The photograph is a close-up of the affected area: 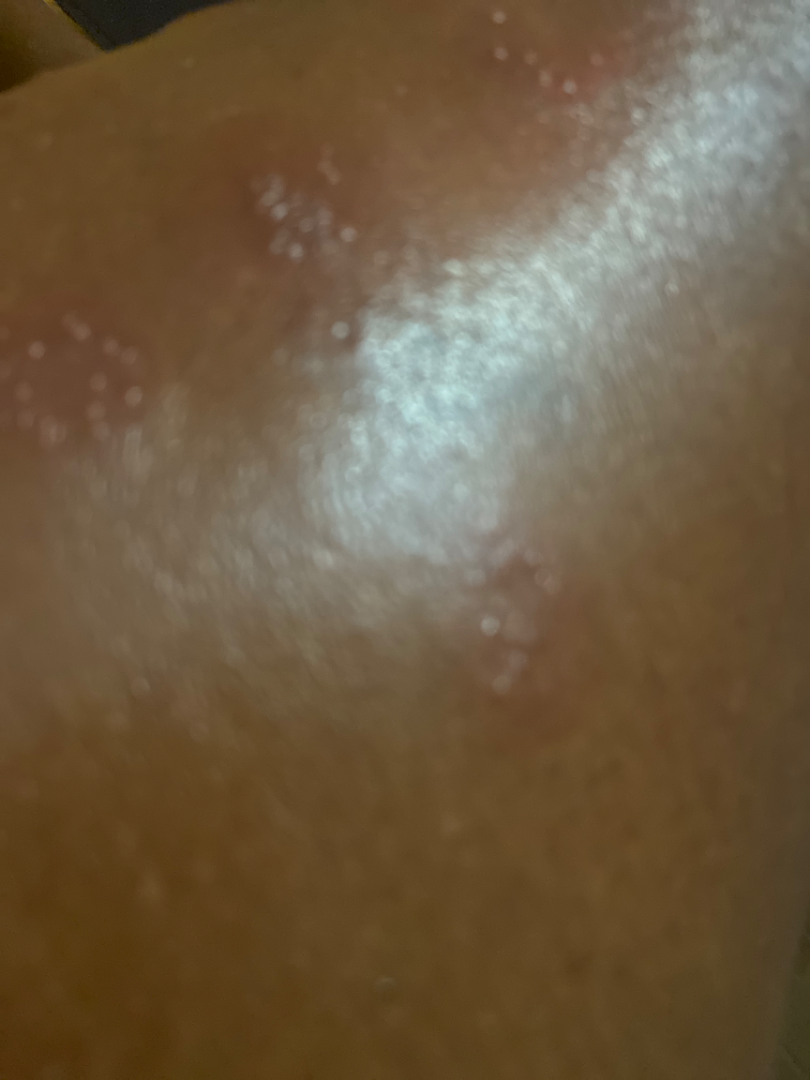  assessment: ungradable on photographic review